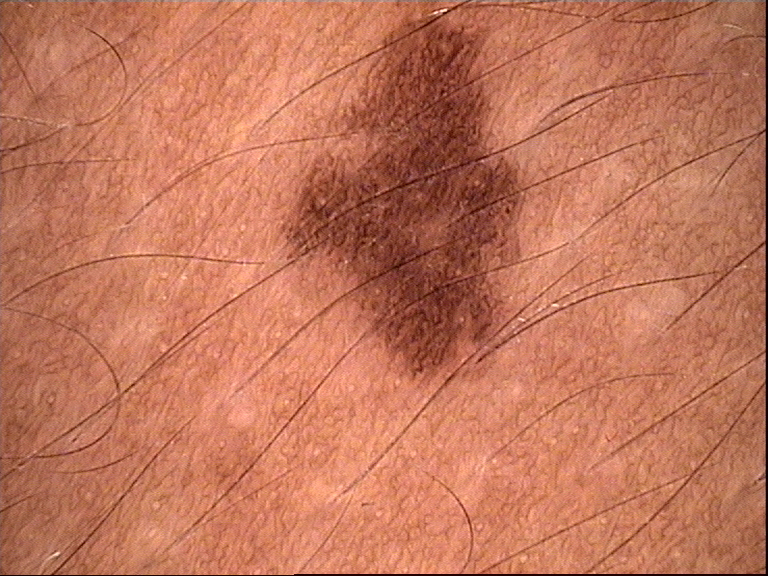Labeled as a dysplastic junctional nevus.